Acquired for a research image collection, with no referral diagnosis · a female patient age 48 · on a questionnaire the patient reported a history of sunbed use and a family history of skin cancer · a macroscopic clinical photograph of a skin lesion · few moles overall by the patient's own estimate · the patient says their skin reddens painfully with sun exposure:
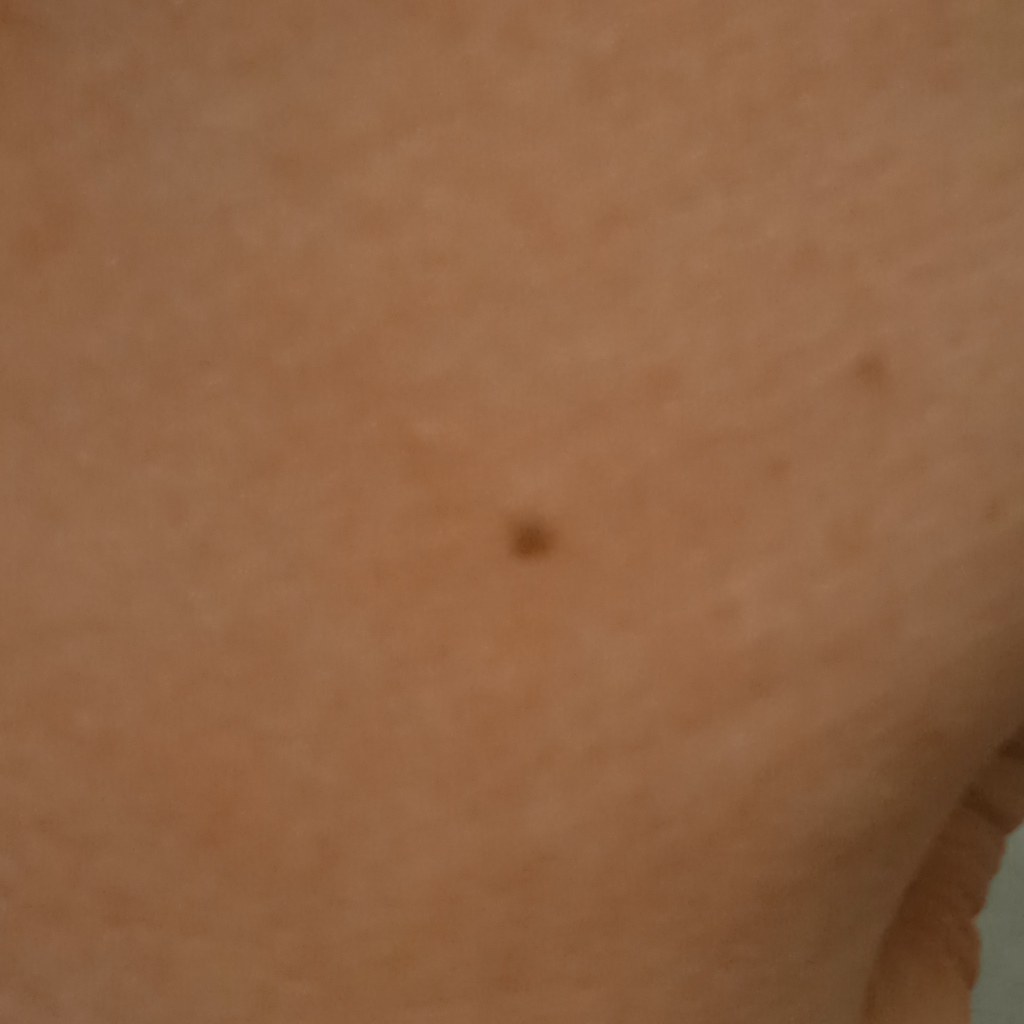Q: How large is the lesion?
A: 2.7 mm
Q: What was the diagnosis?
A: melanocytic nevus (dermatologist consensus)